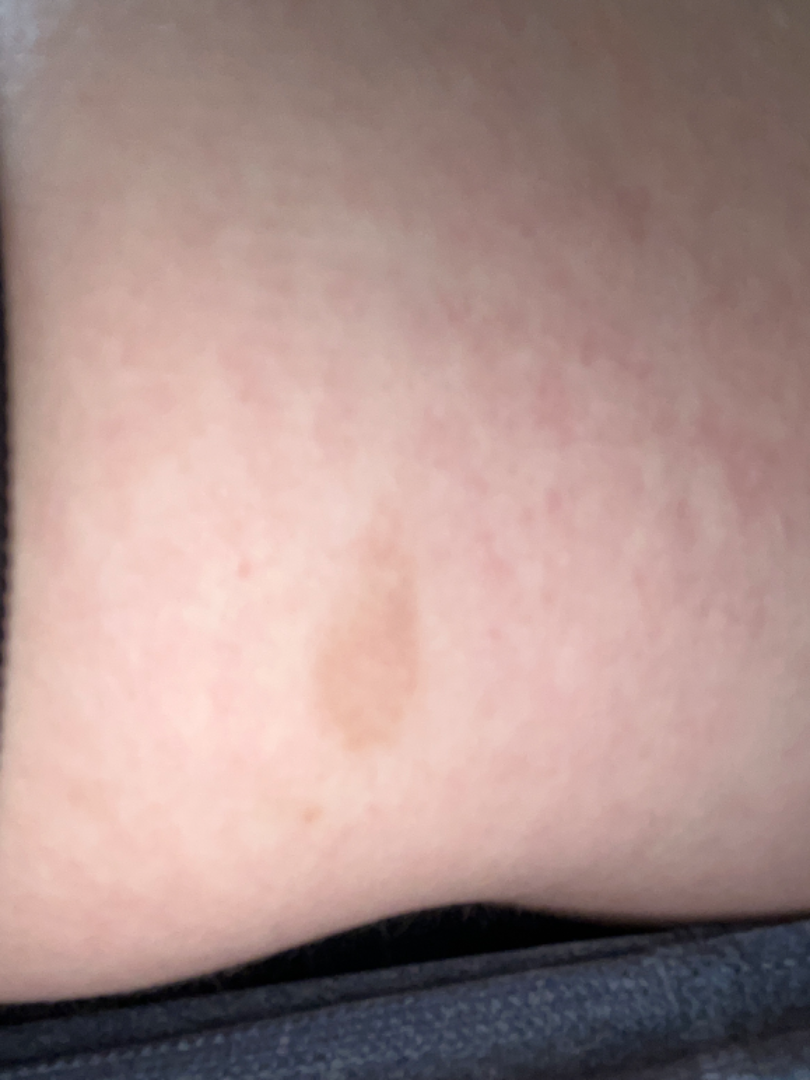assessment — unable to determine.